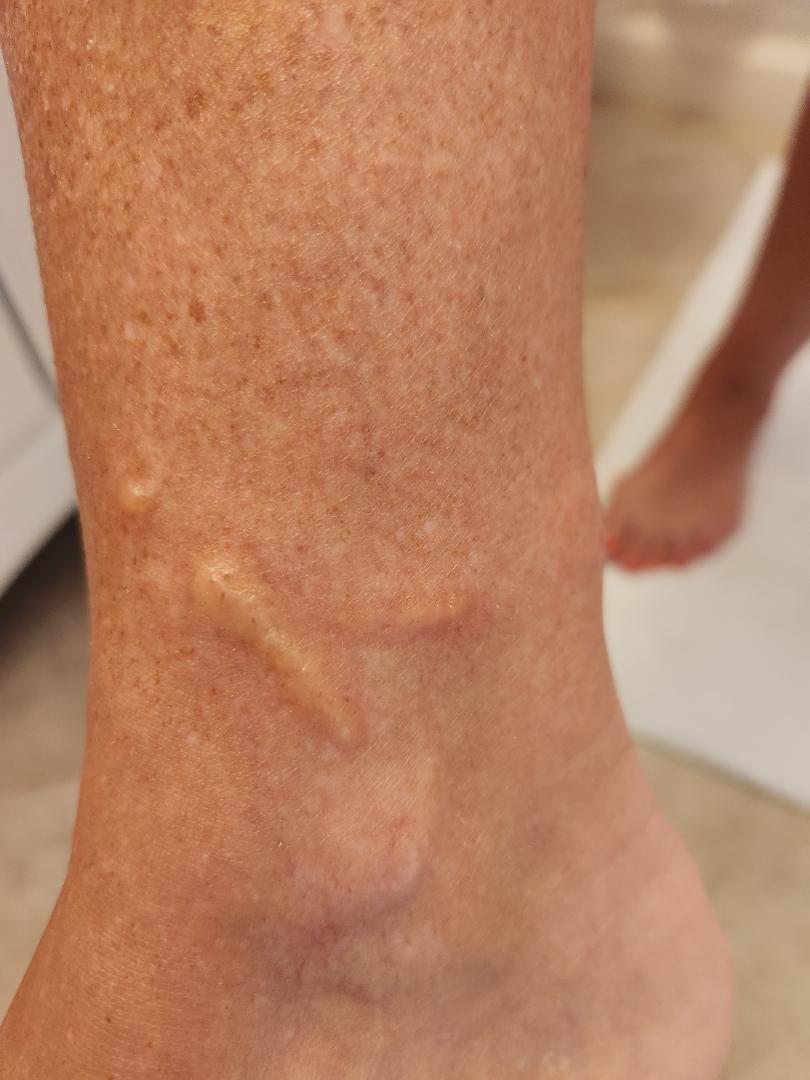{"assessment": "not assessable", "shot_type": "close-up"}